A dermatoscopic image of a skin lesion.
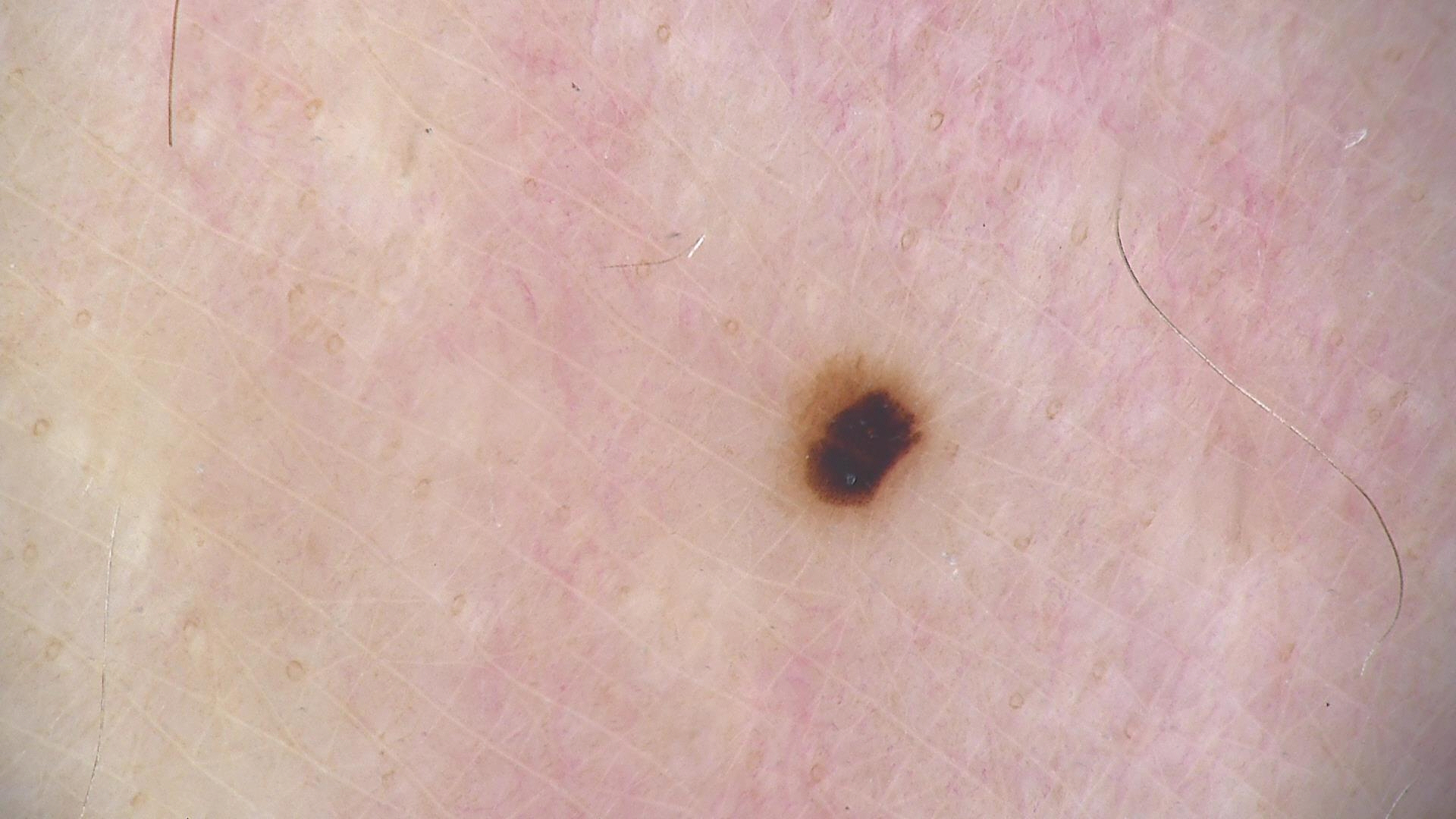Consistent with a benign lesion — an acral dysplastic junctional nevus.